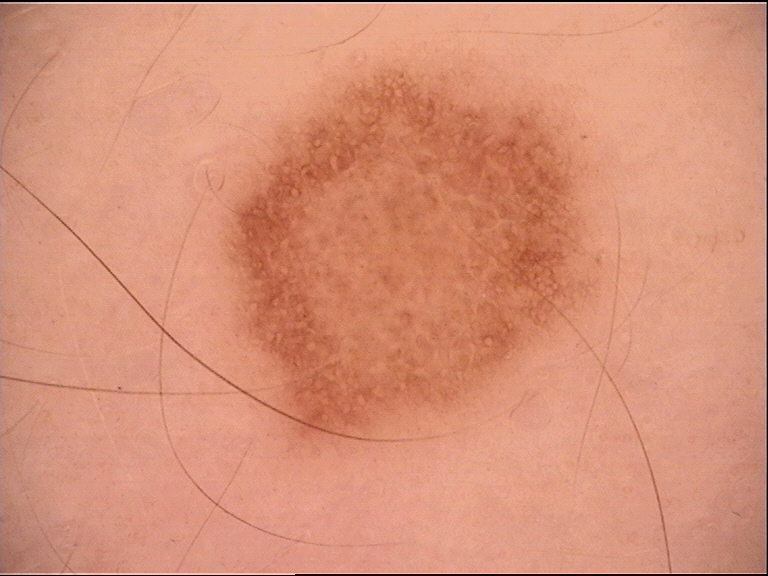Dermoscopy of a skin lesion.
Consistent with a dysplastic junctional nevus.